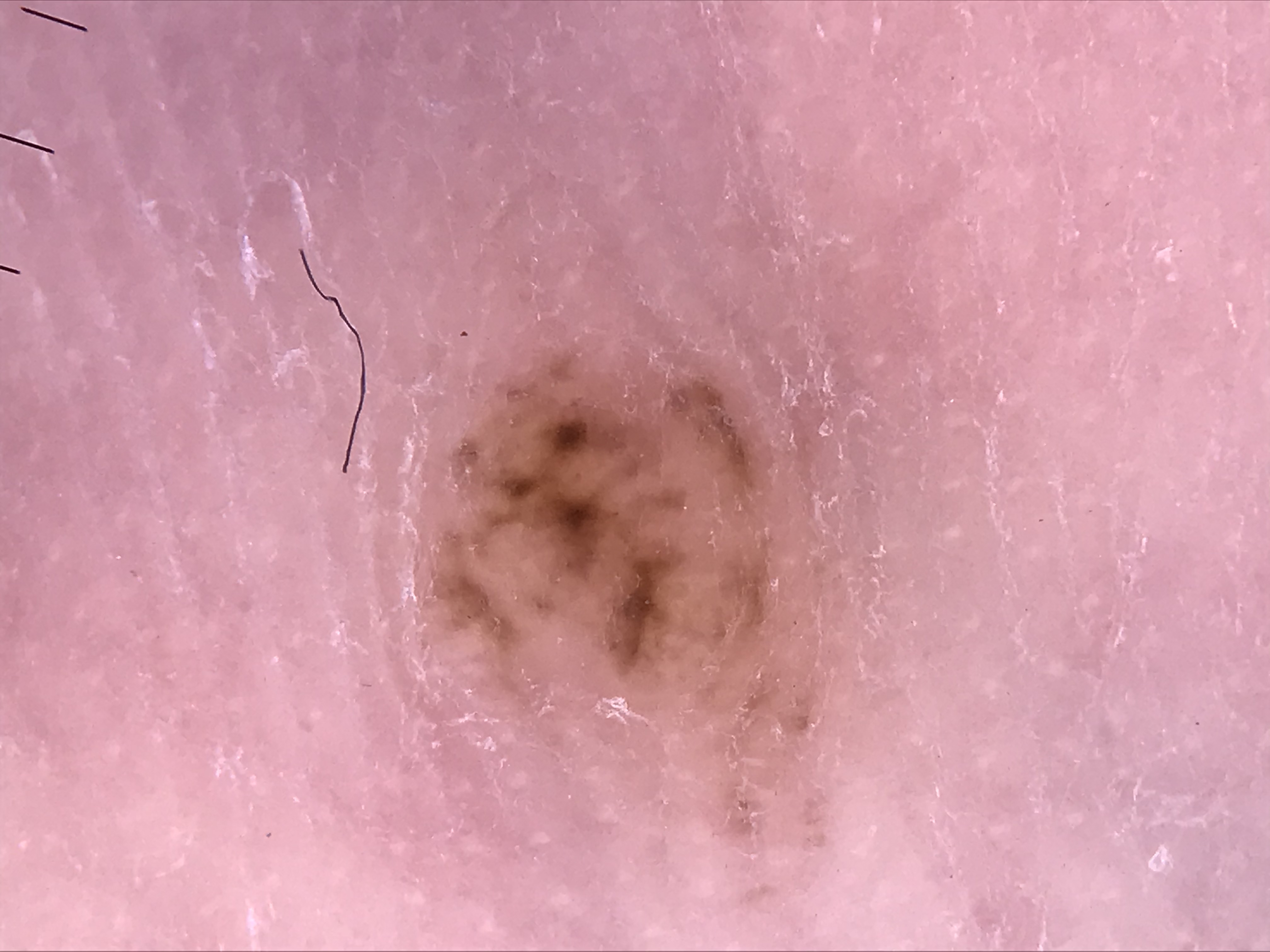{
  "lesion_type": {
    "main_class": "banal",
    "pattern": "compound"
  },
  "diagnosis": {
    "name": "acral compound nevus",
    "code": "acb",
    "malignancy": "benign",
    "super_class": "melanocytic",
    "confirmation": "expert consensus"
  }
}